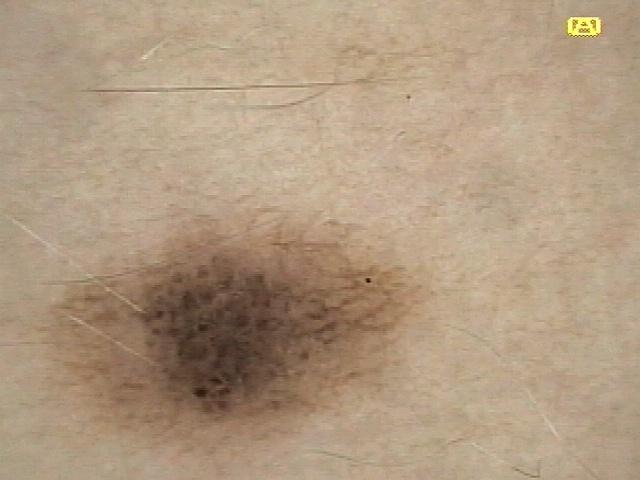Q: What are the patient's age and sex?
A: female, about 20 years old
Q: Where is the lesion located?
A: an upper extremity
Q: What is this lesion?
A: Nevus